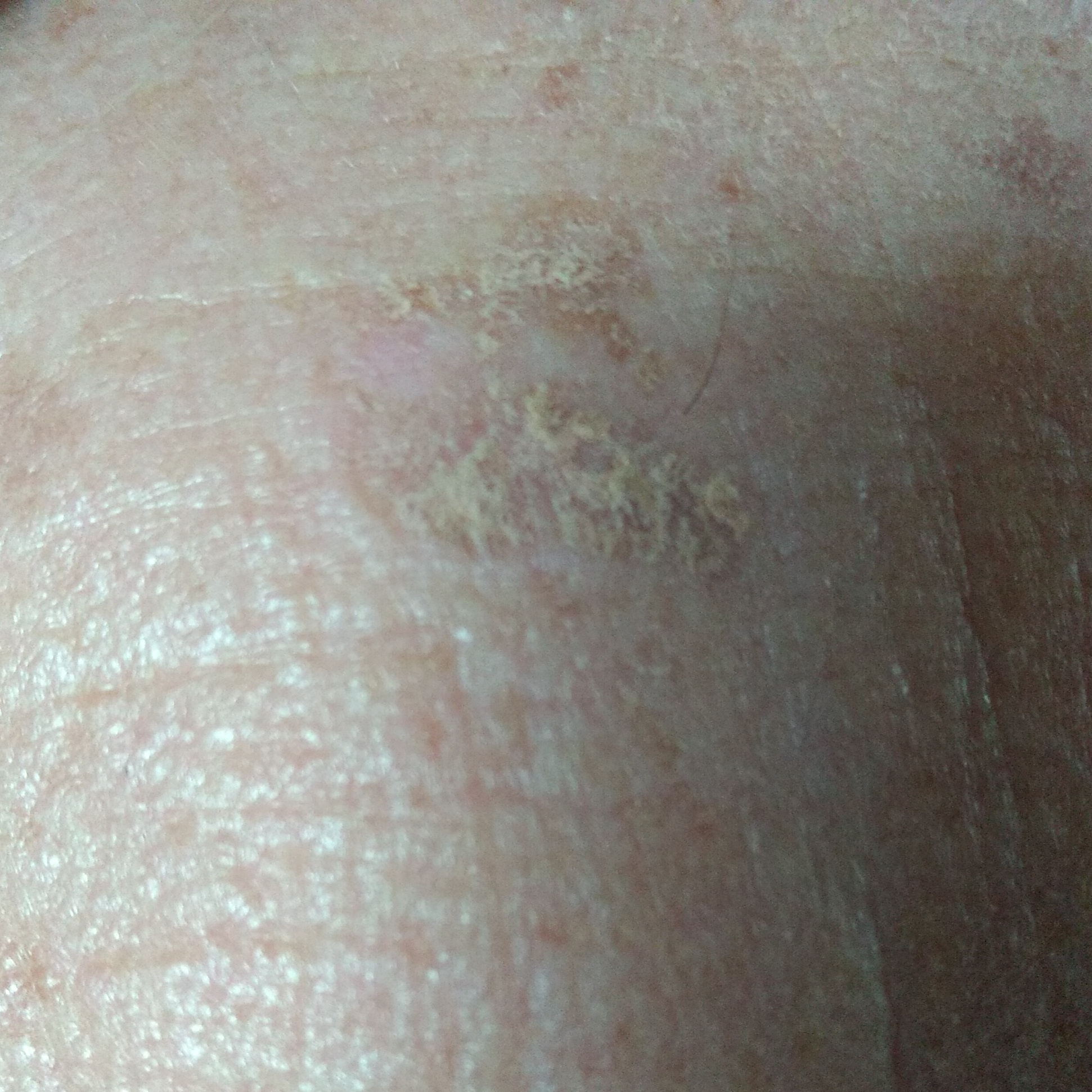{"patient": {"age": 68}, "image": "smartphone clinical photo", "lesion_location": "the face", "symptoms": {"present": ["elevation"], "absent": ["change in appearance"]}, "diagnosis": {"name": "actinic keratosis", "code": "ACK", "malignancy": "indeterminate", "confirmation": "clinical consensus"}}